A female subject roughly 80 years of age — 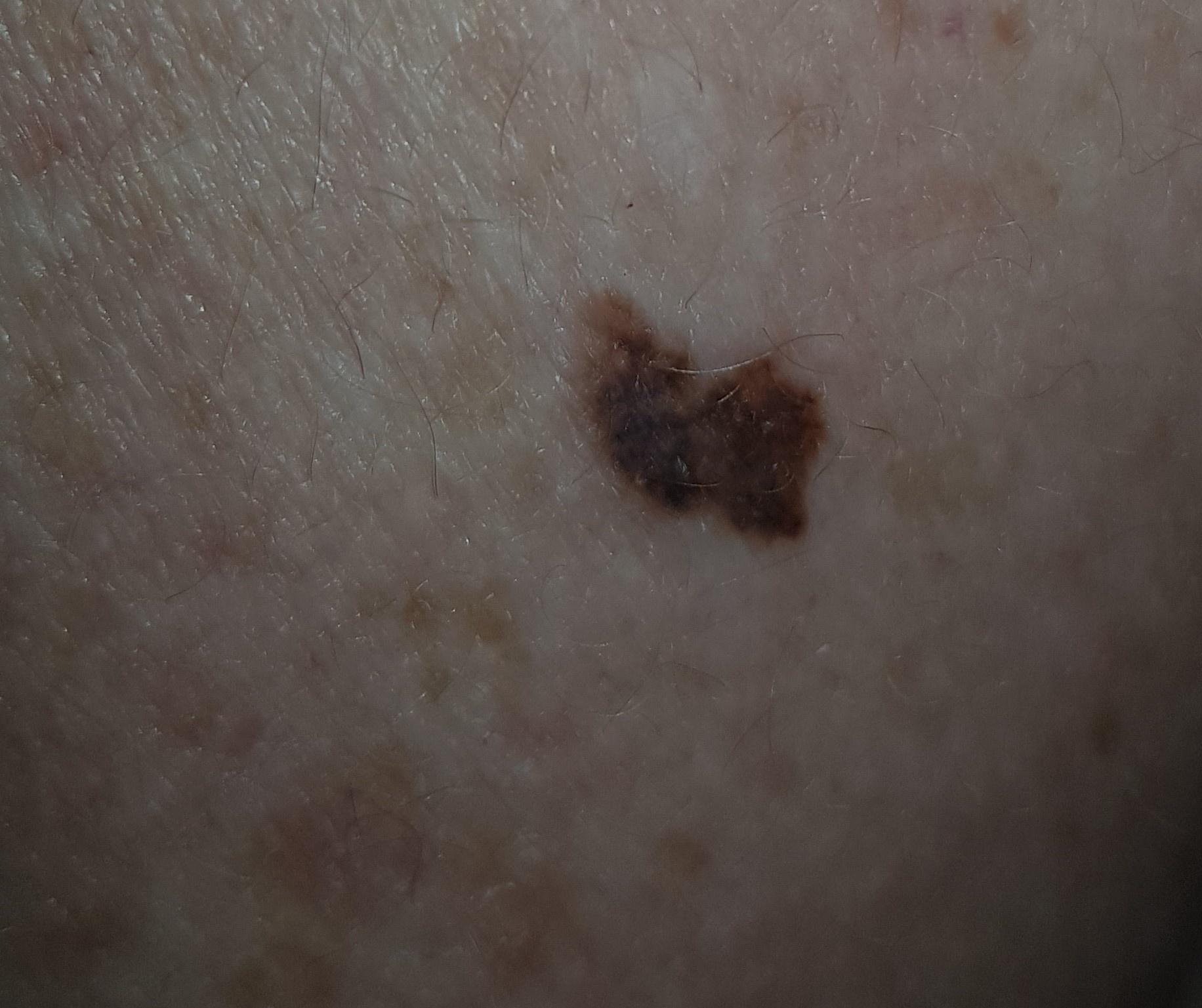Case:
- diagnosis: Nevus (biopsy-proven)